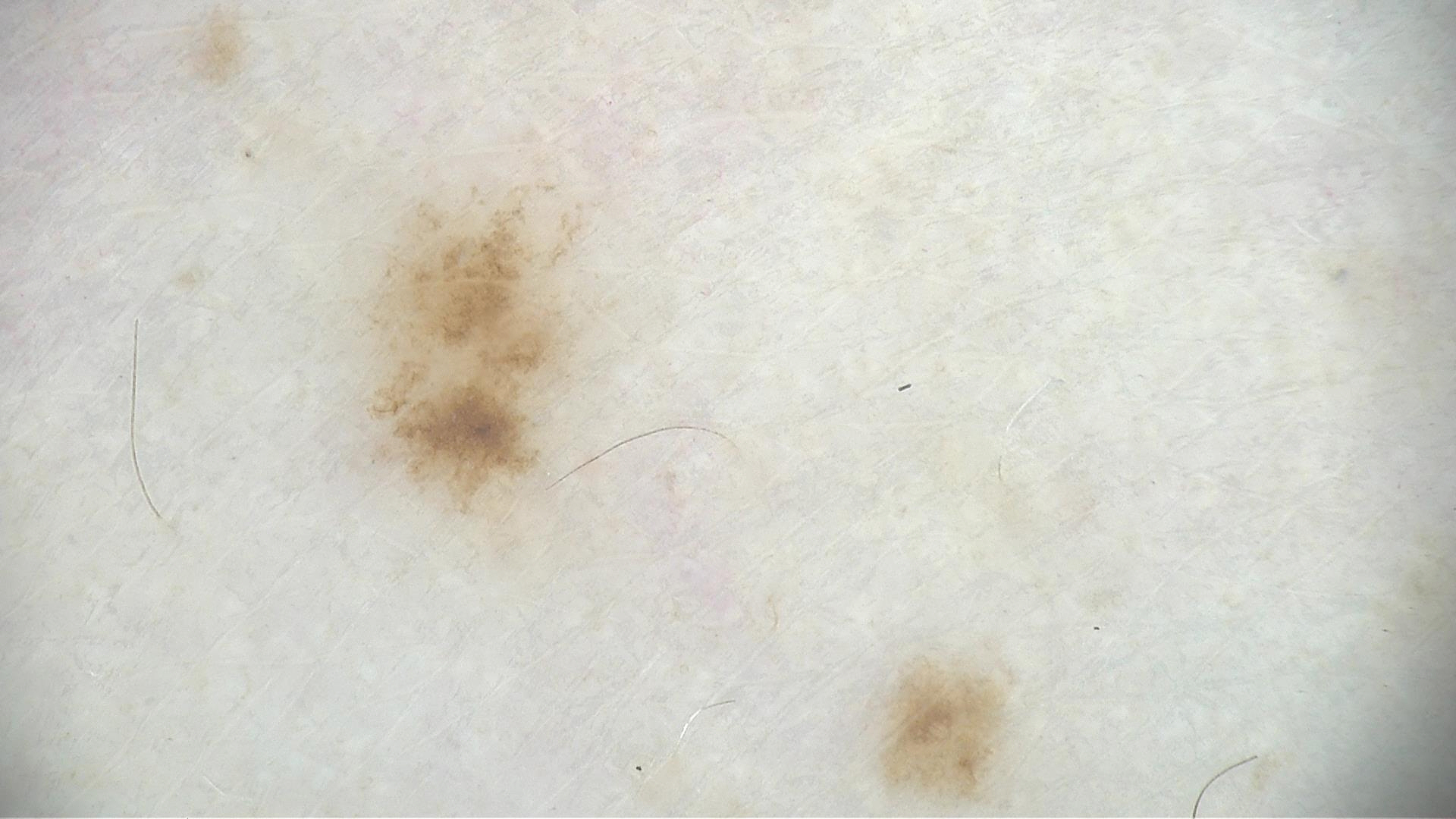A skin lesion imaged with a dermatoscope. Diagnosed as a dysplastic junctional nevus.